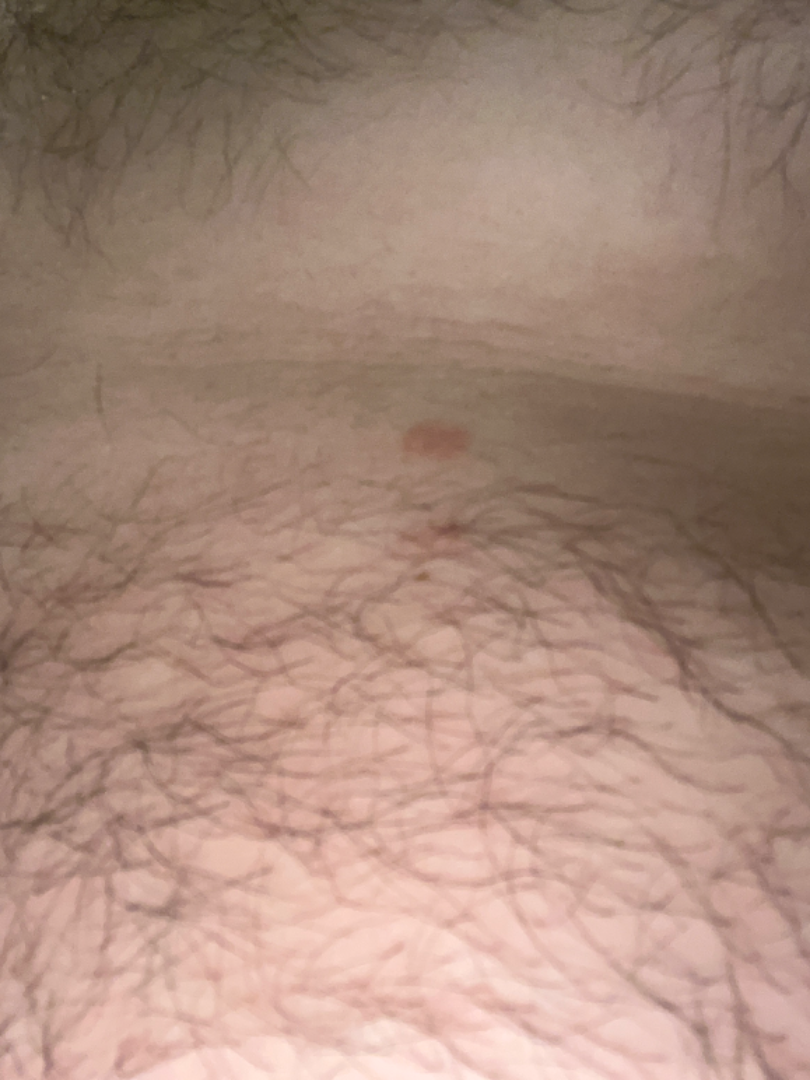| feature | finding |
|---|---|
| assessment | indeterminate from the photograph |
| subject | male, age 18–29 |
| image framing | close-up |
| site | front of the torso |